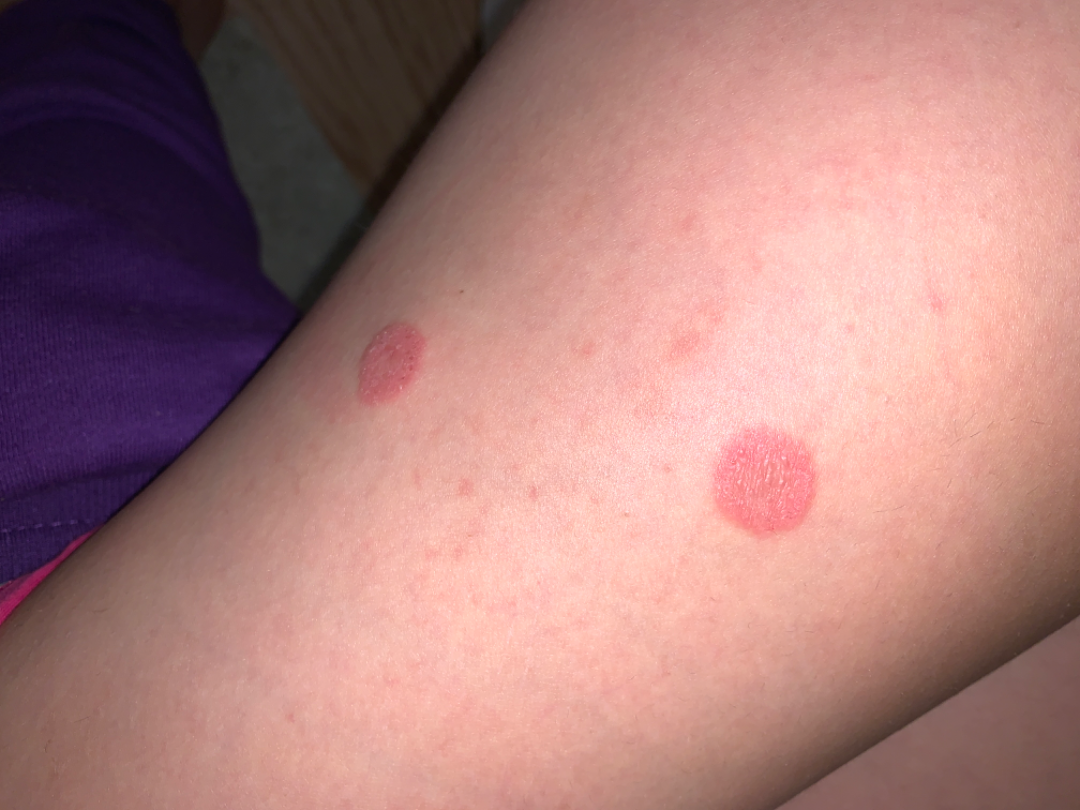Assessment:
On remote review of the image: favoring Eczema; an alternative is Lichen Simplex Chronicus; also consider Psoriasis.